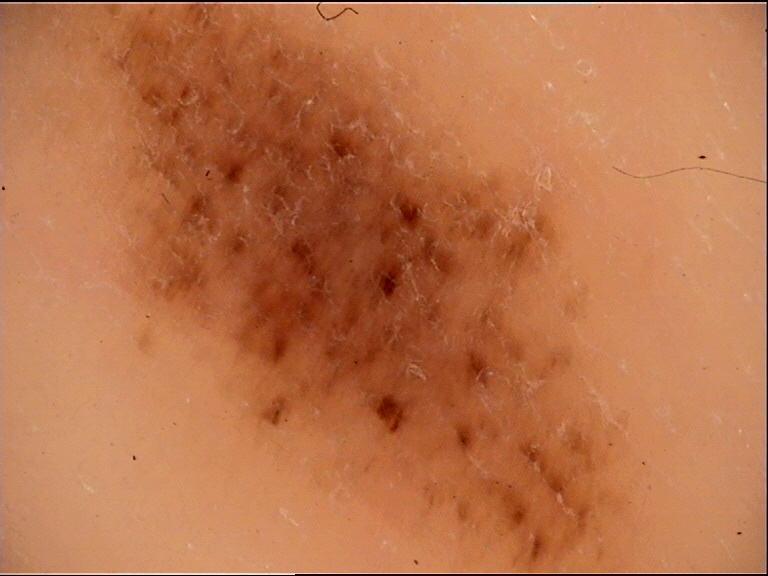diagnosis — acral dysplastic junctional nevus (expert consensus).